History notes prior malignancy (patient or family), pesticide exposure, and no tobacco use.
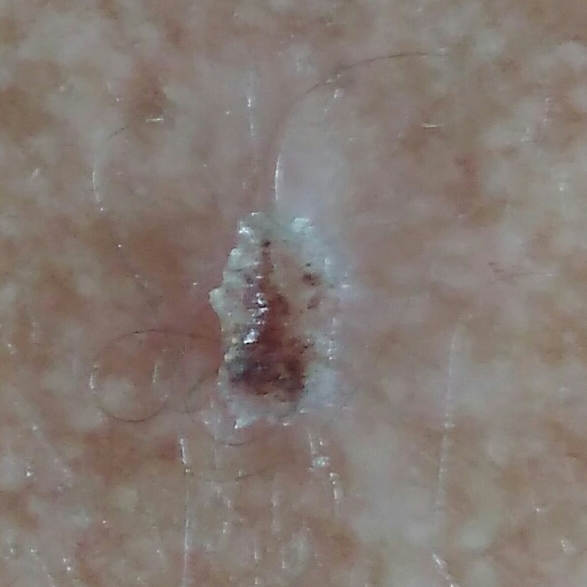reported symptoms: itching / no change in appearance, no bleeding | pathology: actinic keratosis (biopsy-proven).